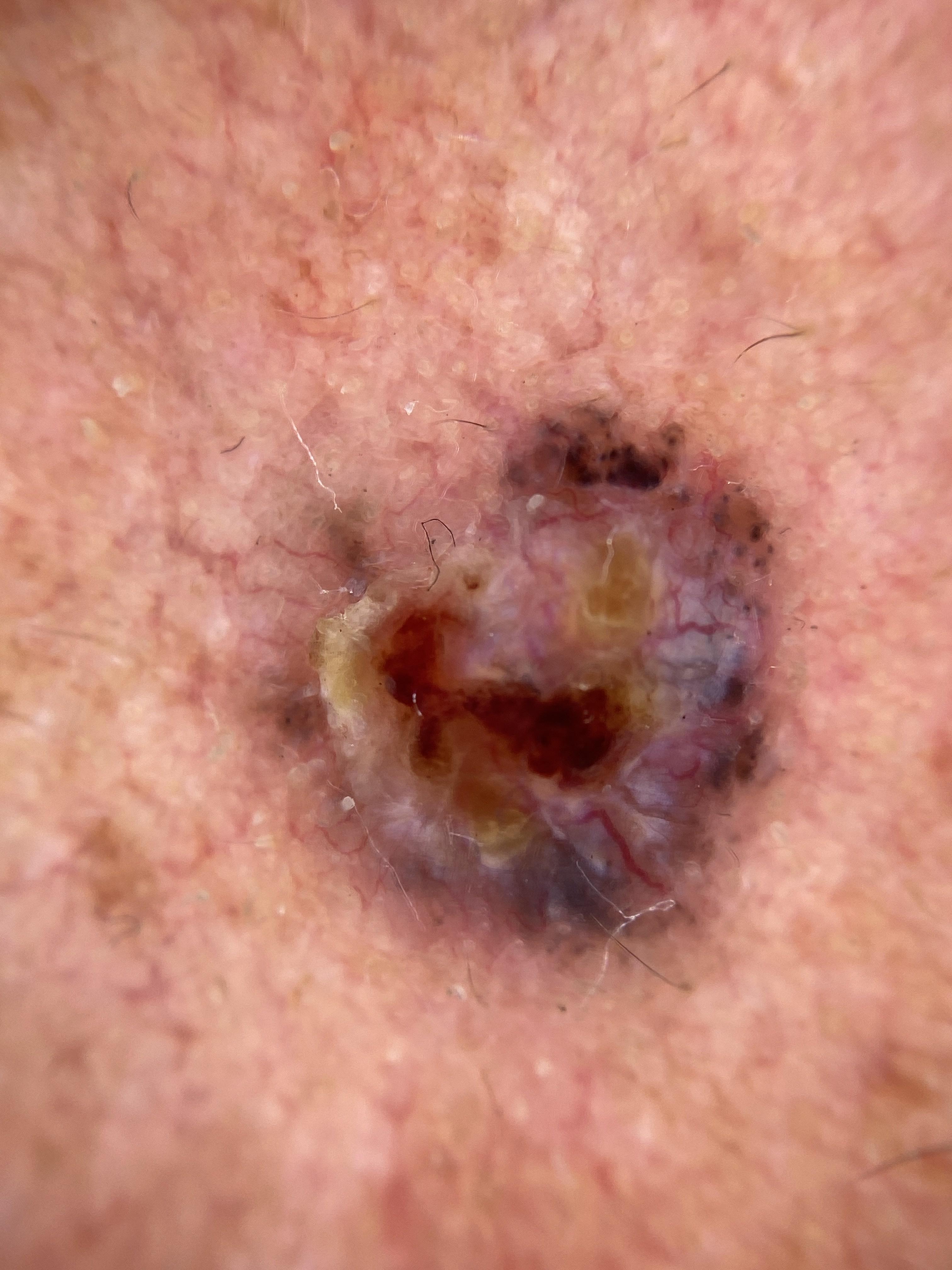Notes:
– skin phototype: II
– modality: dermoscopy
– subject: male, aged 73 to 77
– location: the head or neck
– diagnosis: Basal cell carcinoma (biopsy-proven)